The lesion involves the arm, leg, top or side of the foot and back of the torso; female patient, age 50–59; the photograph was taken at a distance.
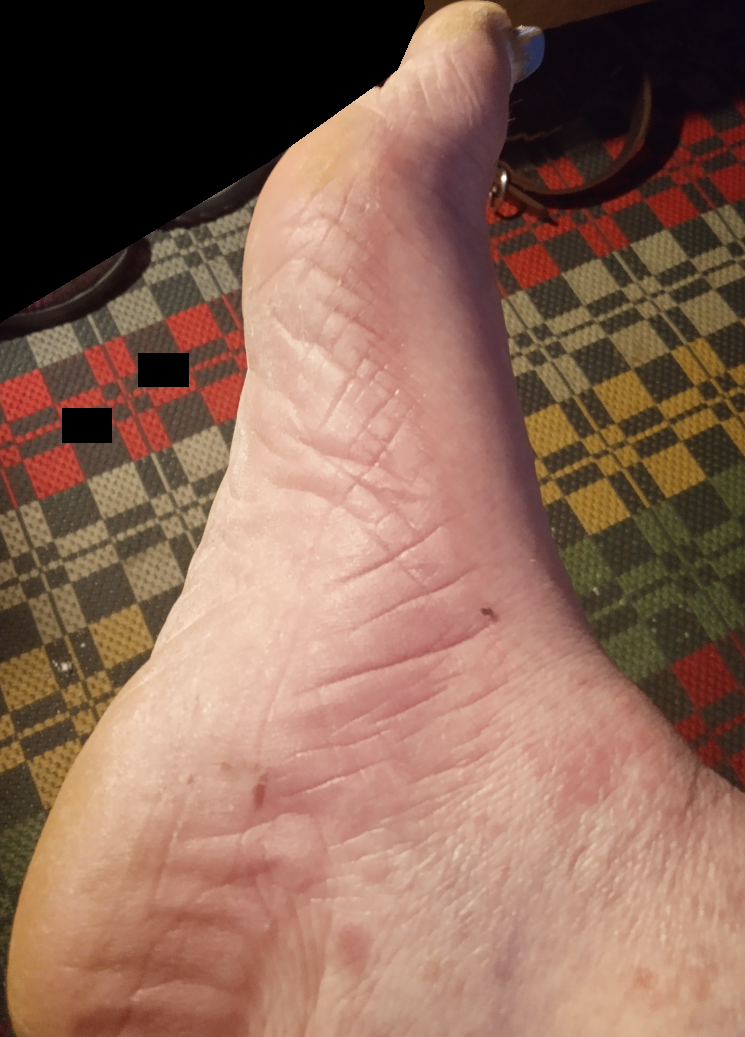Q: What is the differential diagnosis?
A: most likely Keratoderma; also consider Hyperkeratosis